A dermoscopic image of a skin lesion.
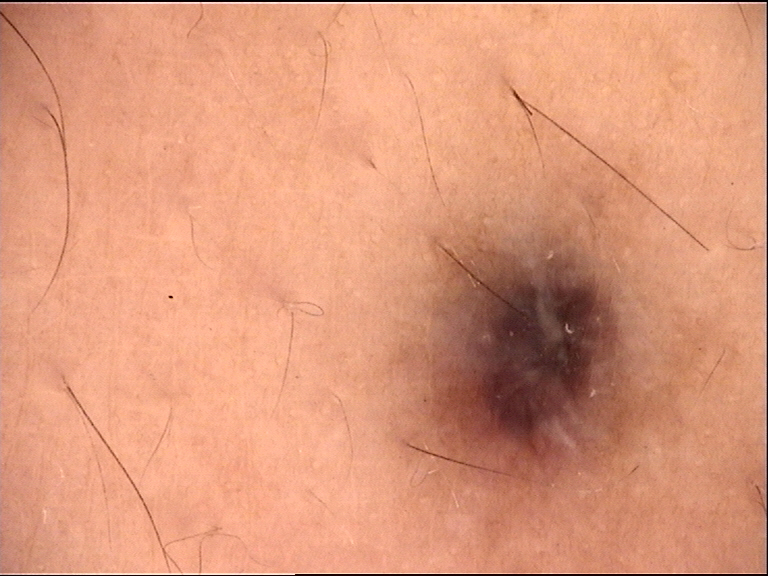Q: What is the lesion category?
A: banal, dermal
Q: What is the diagnosis?
A: blue nevus (expert consensus)